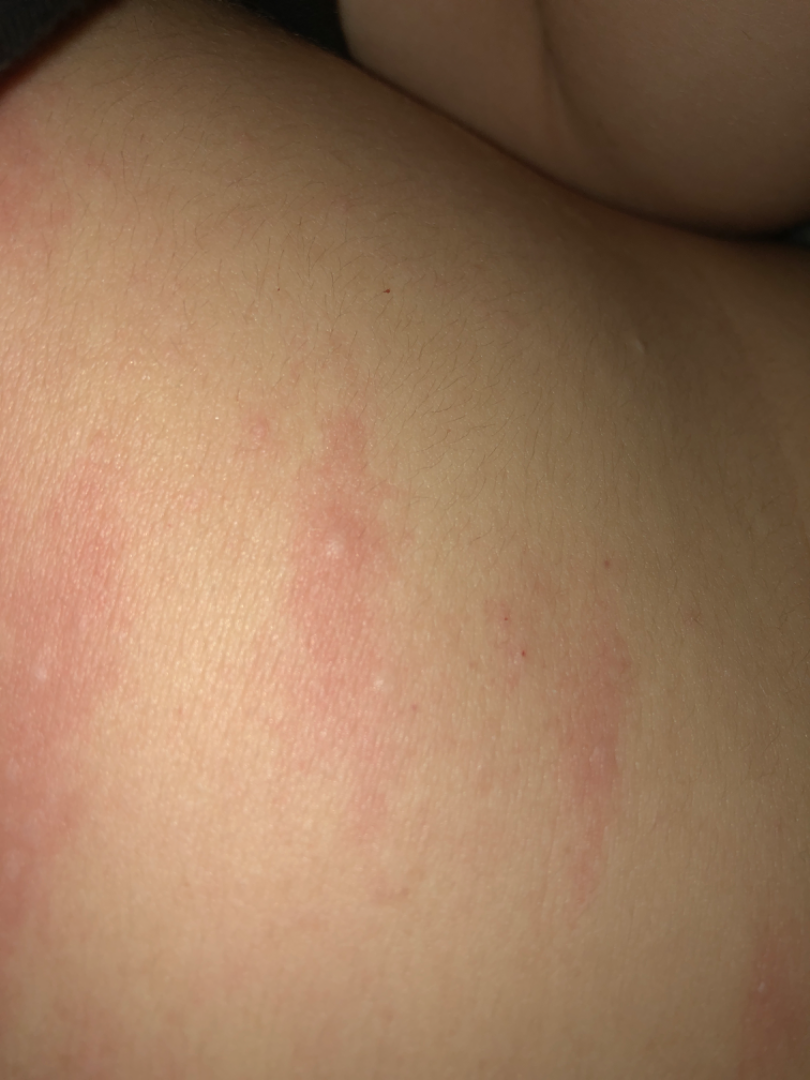One reviewing dermatologist: Urticaria and Eczema were each considered, in no particular order.